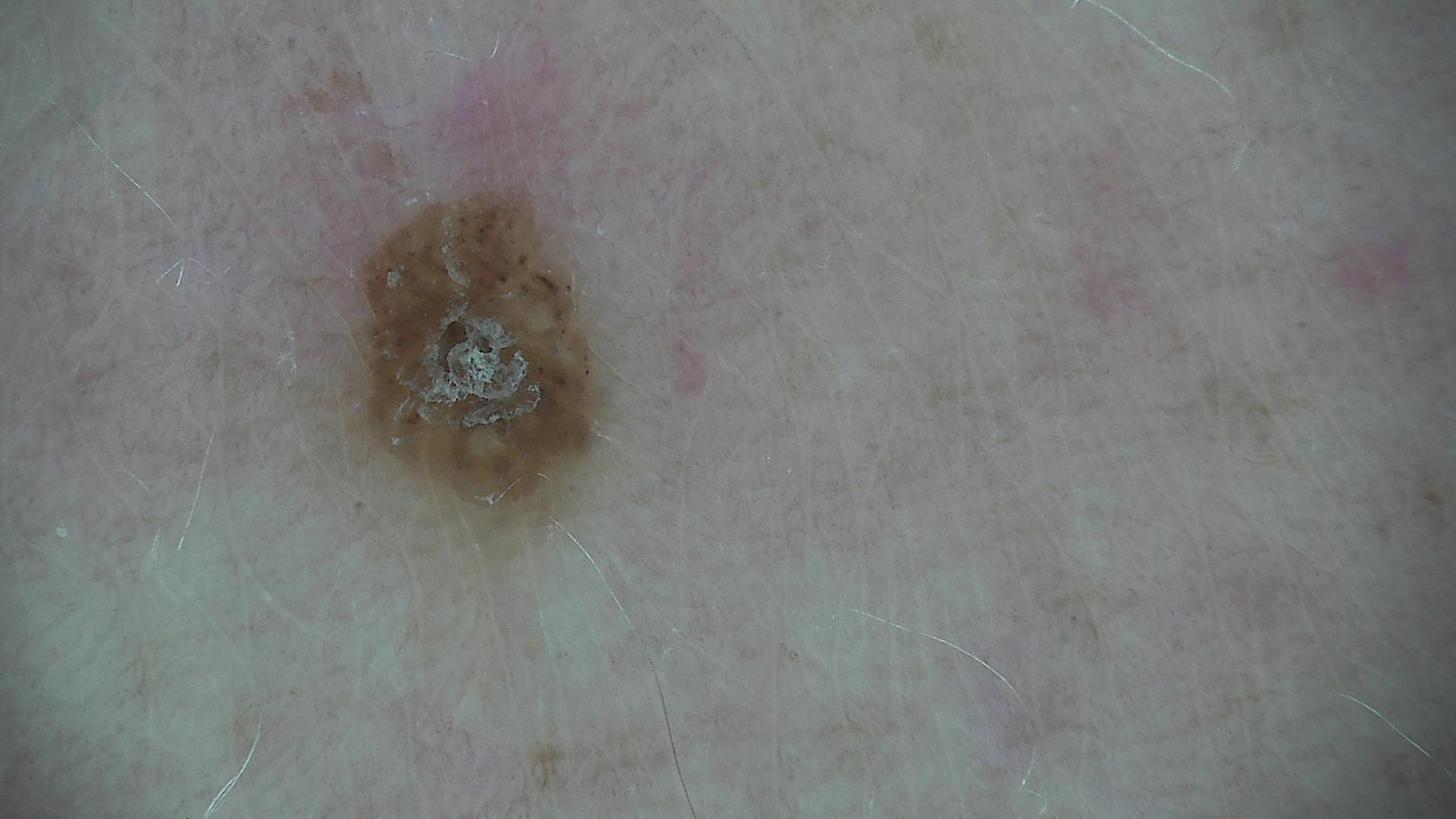subtype=keratinocytic
label=seborrheic keratosis (expert consensus)